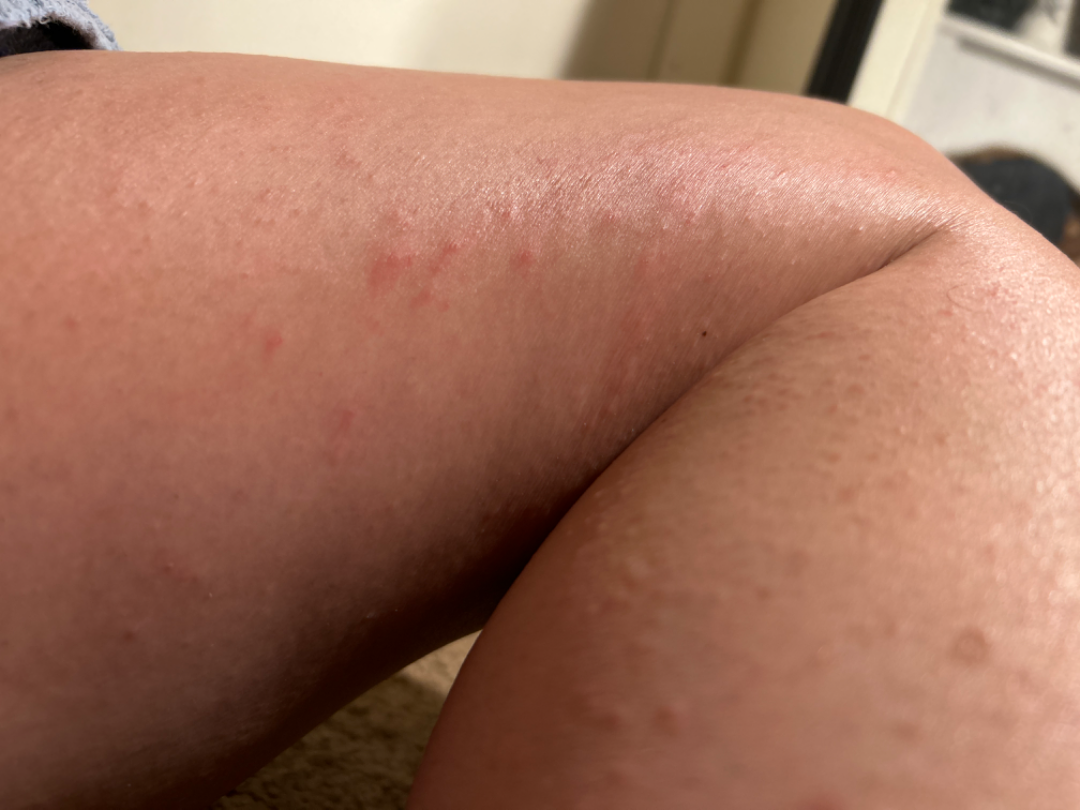Review:
The skin findings could not be characterized from the image.
Patient information:
Reported lesion symptoms include itching. Self-categorized by the patient as skin that appeared healthy to them. The contributor reports the lesion is raised or bumpy. The photo was captured at an angle. The lesion involves the arm and leg.